Dermoscopy of a skin lesion · a female subject, in their 60s.
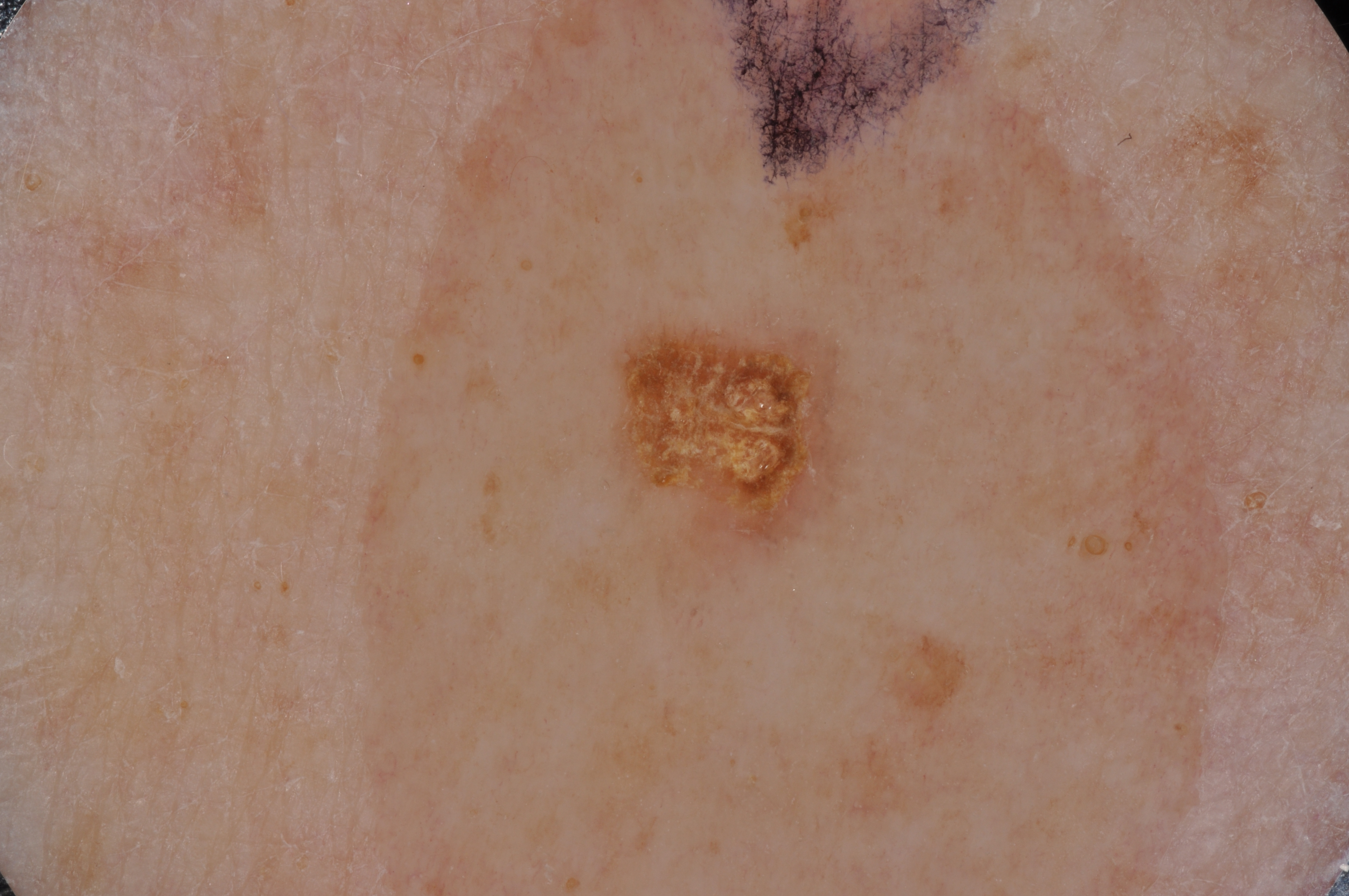Case summary:
Dermoscopic examination shows no milia-like cysts, streaks, negative network, or pigment network. The lesion occupies the region left=611, top=329, right=843, bottom=560.
Impression:
Expert review diagnosed this as a seborrheic keratosis, a benign lesion.